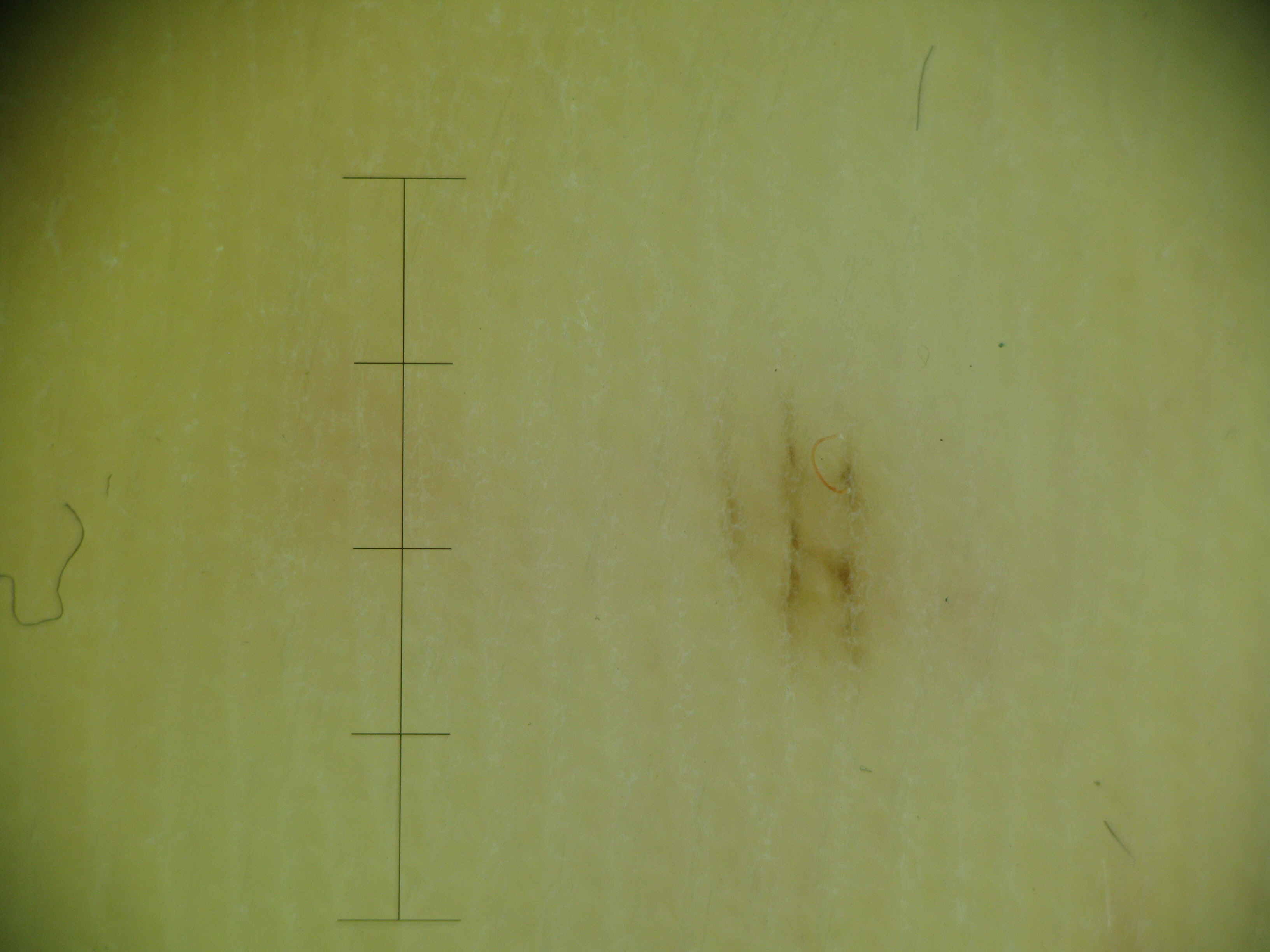Q: What is the imaging modality?
A: dermoscopy
Q: What was the diagnostic impression?
A: acral junctional nevus (expert consensus)